A dermoscopic image of a skin lesion.
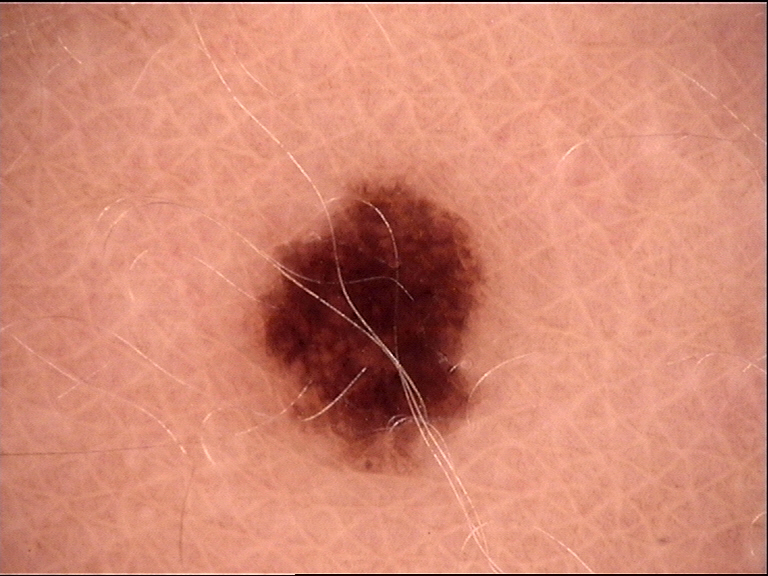Consistent with a dysplastic junctional nevus.